Fitzpatrick I; the chart records prior malignancy (patient or family), no alcohol use, and no prior skin cancer (patient or family); a female patient age 92; a clinical photo of a skin lesion taken with a smartphone: 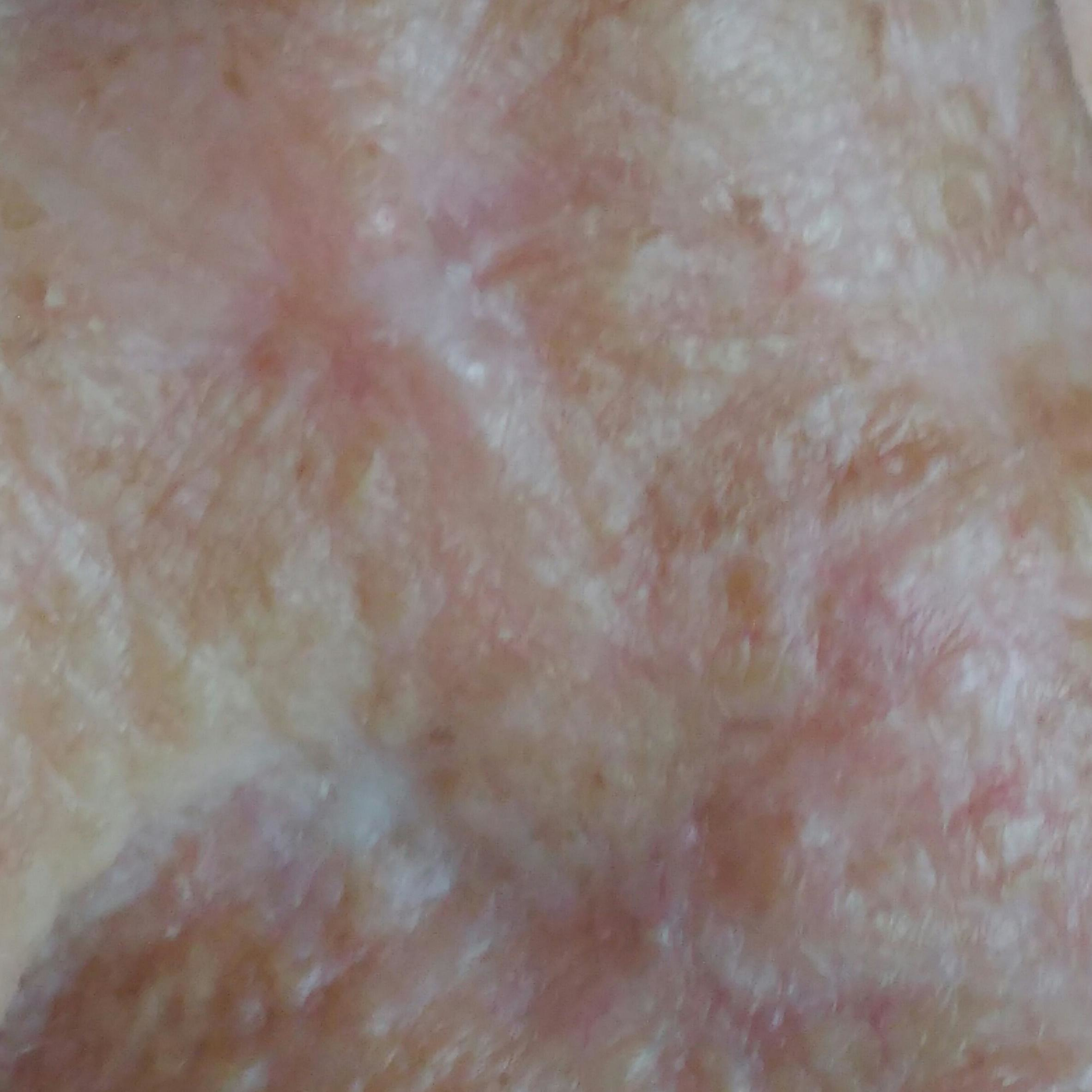The lesion involves the nose. The lesion is roughly 5 by 3 mm. Histopathological examination showed a malignant skin lesion — a squamous cell carcinoma.